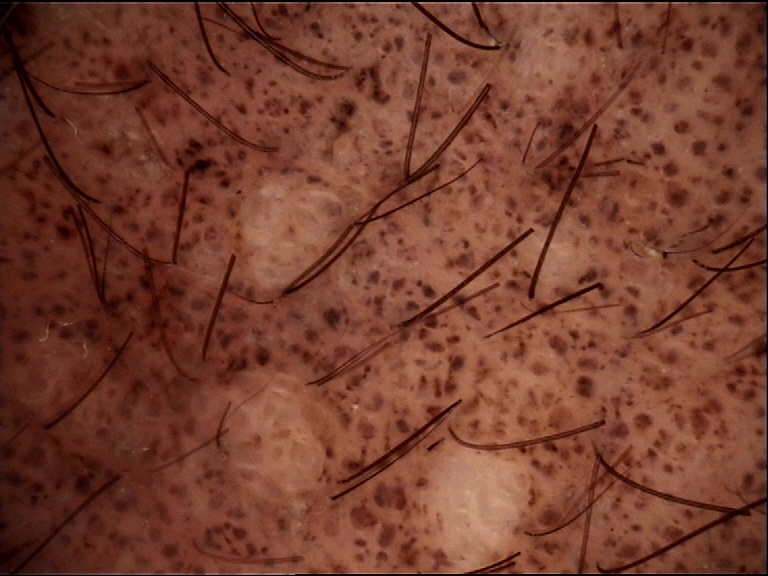Q: What kind of image is this?
A: dermatoscopy
Q: What is the diagnosis?
A: congenital compound nevus (expert consensus)